A dermoscopy image of a single skin lesion:
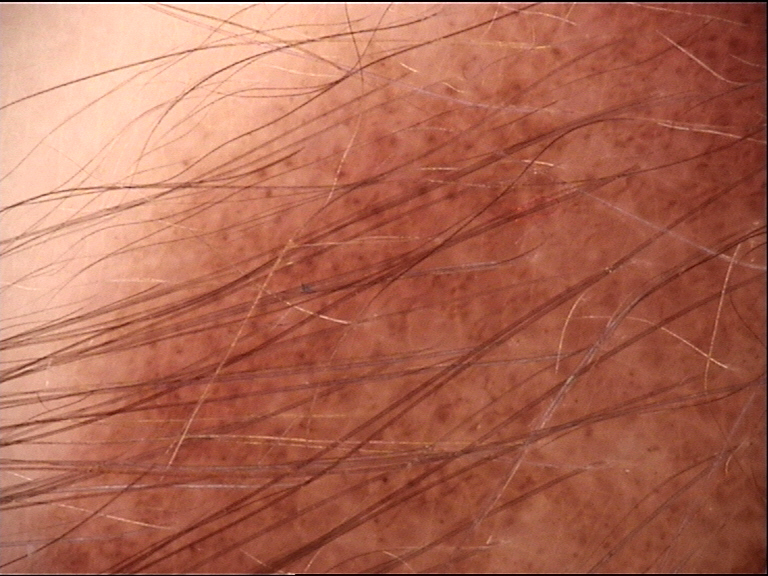{
  "diagnosis": {
    "name": "congenital junctional nevus",
    "code": "cjb",
    "malignancy": "benign",
    "super_class": "melanocytic",
    "confirmation": "expert consensus"
  }
}